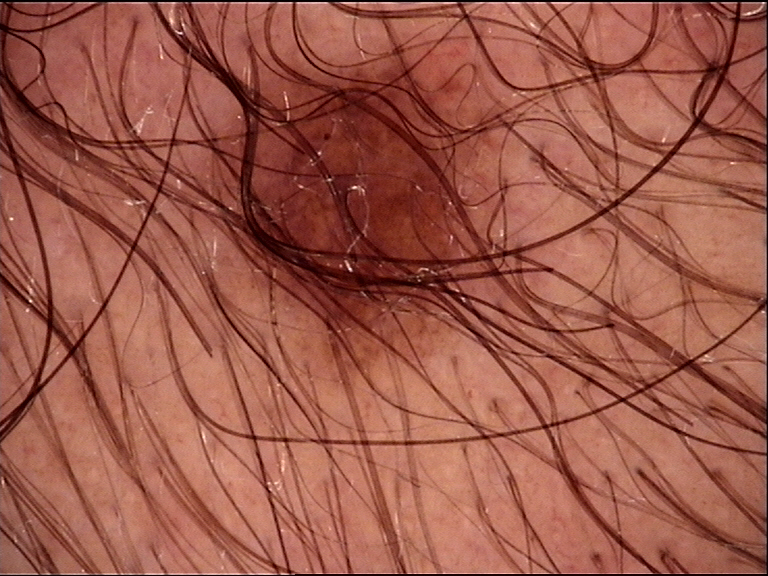imaging: dermoscopy | label: compound nevus (expert consensus).